Dermoscopy of a skin lesion.
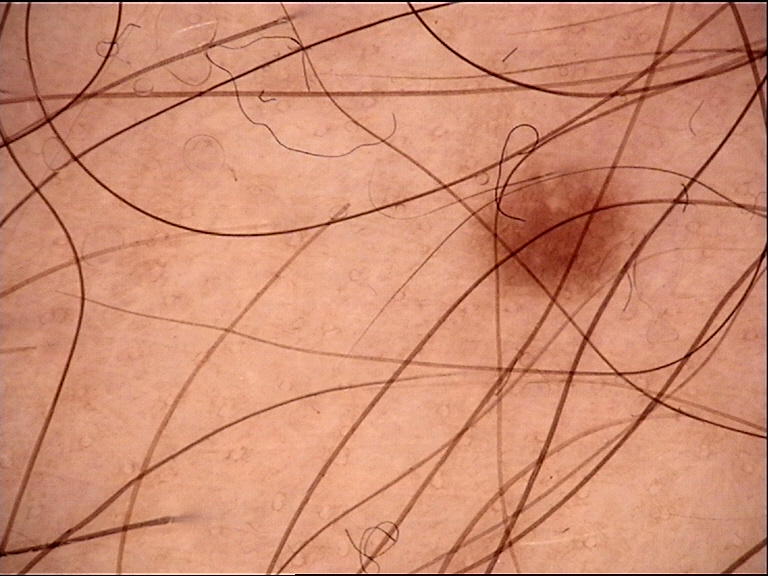Conclusion:
Consistent with a banal lesion — a junctional nevus.